The patient described the issue as a rash, the lesion is associated with burning and itching, texture is reported as raised or bumpy, located on the back of the hand and palm, the photo was captured at an angle, no associated systemic symptoms reported, the condition has been present for less than one week: 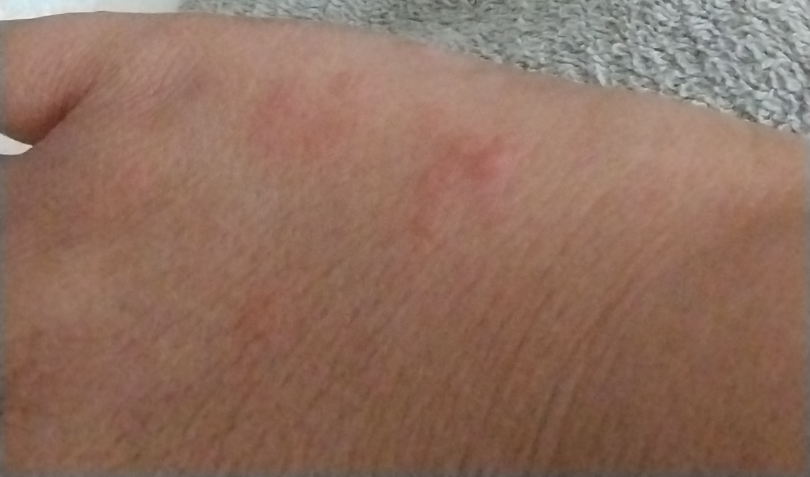Reviewed remotely by one dermatologist: most consistent with Urticaria; an alternative is Granuloma annulare.